A dermoscopy image of a single skin lesion:
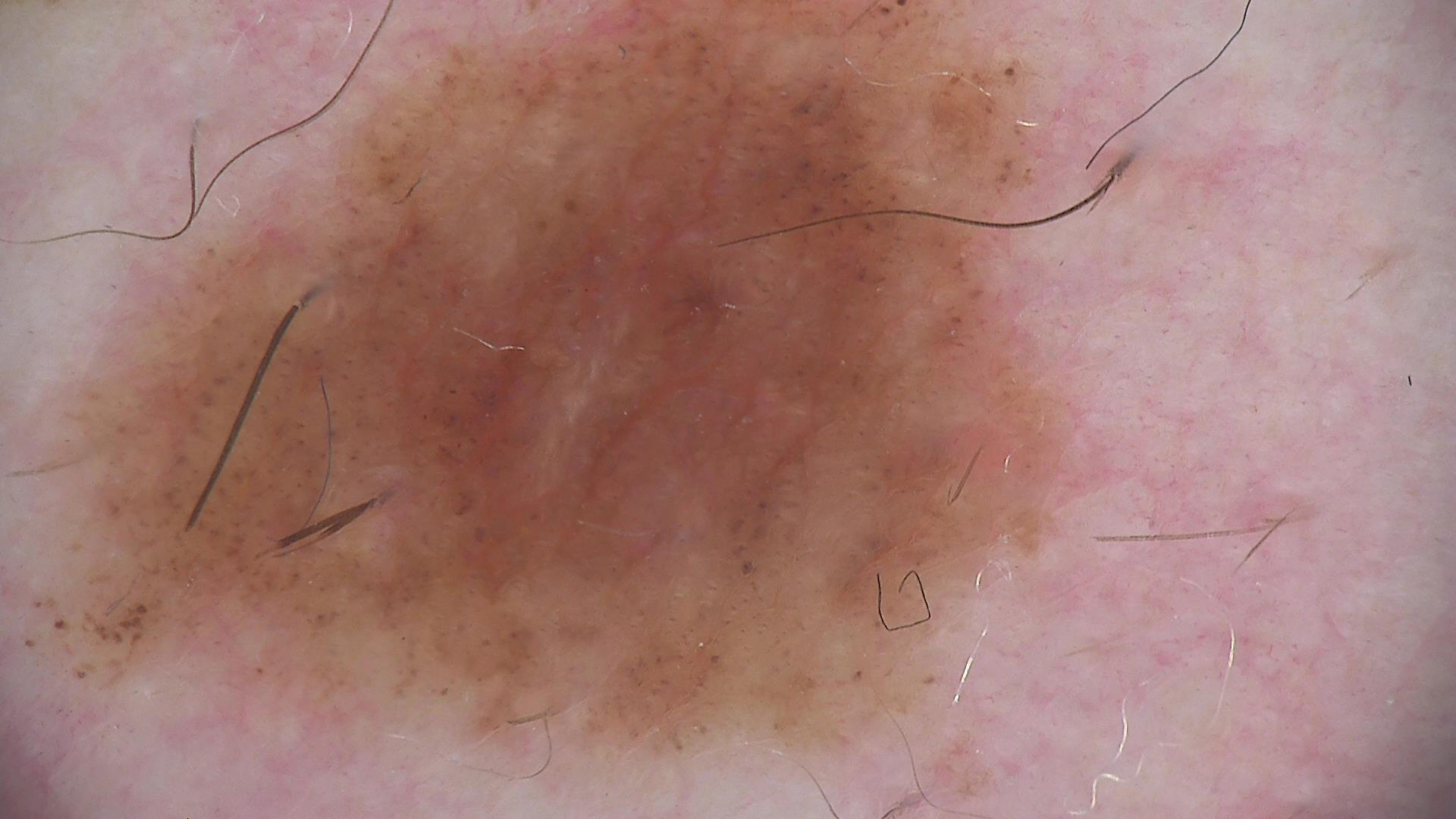label: dysplastic compound nevus (expert consensus).